A dermatoscopic image of a skin lesion · a male subject aged around 70 · recorded as FST II: 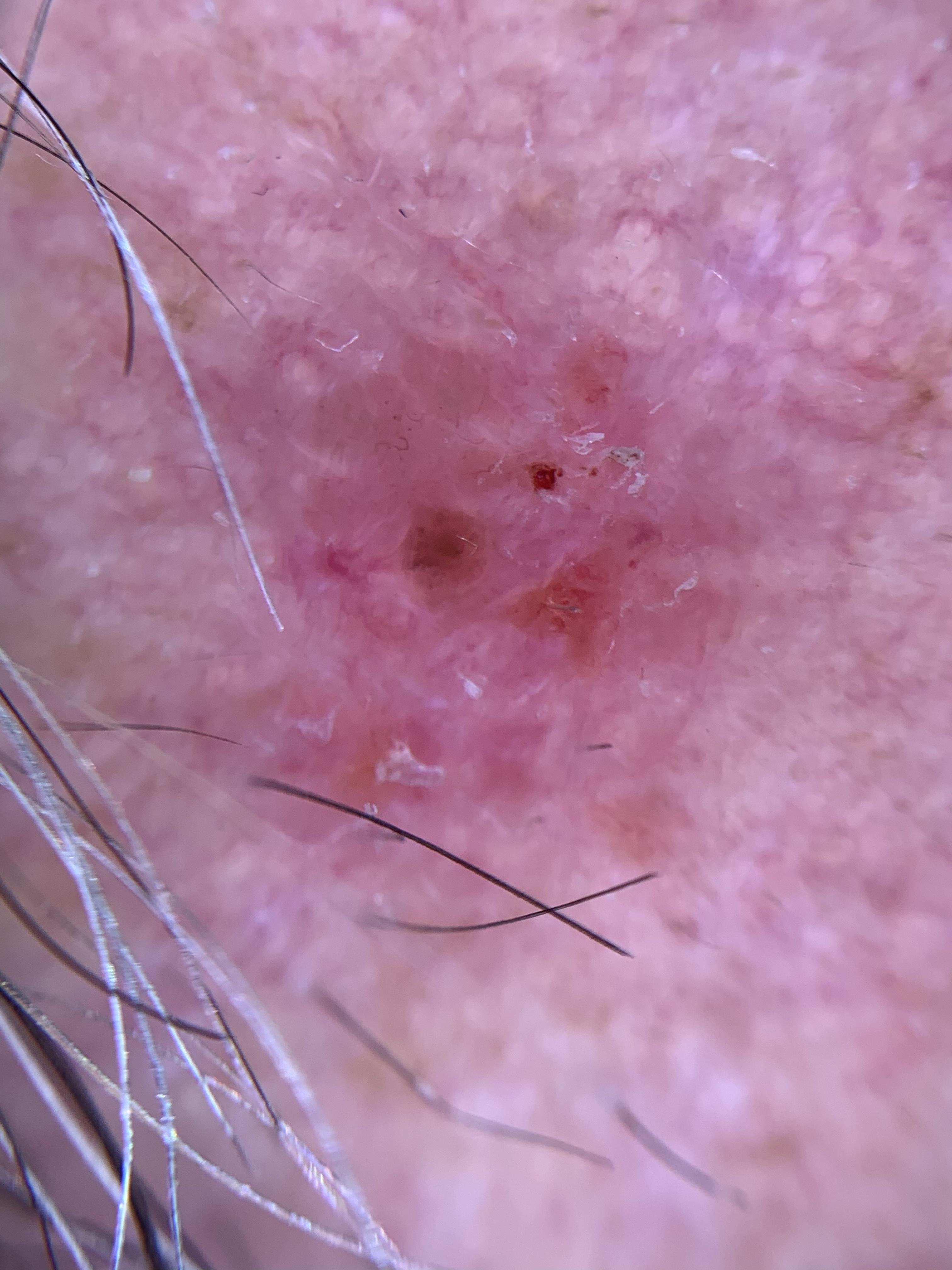<lesion>
<lesion_location>
<region>the head or neck</region>
</lesion_location>
<diagnosis>
<name>Basal cell carcinoma</name>
<malignancy>malignant</malignancy>
<confirmation>histopathology</confirmation>
<lineage>adnexal</lineage>
</diagnosis>
</lesion>